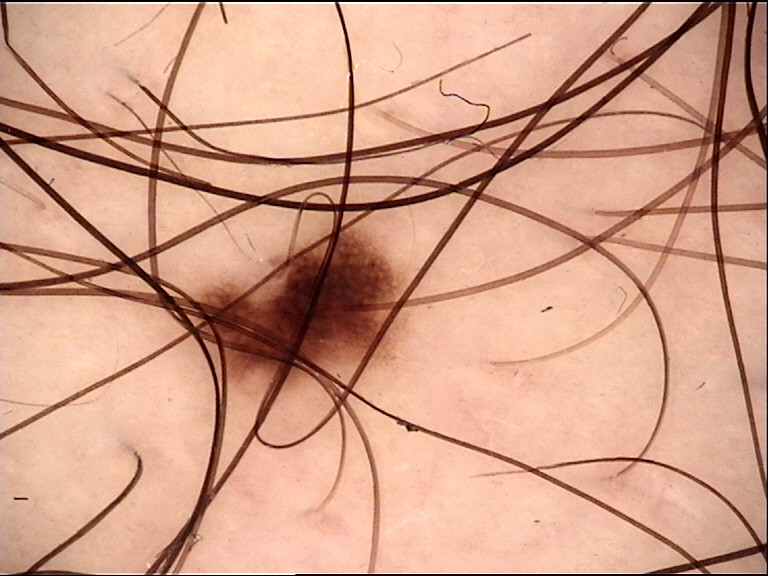diagnosis — junctional nevus (expert consensus)